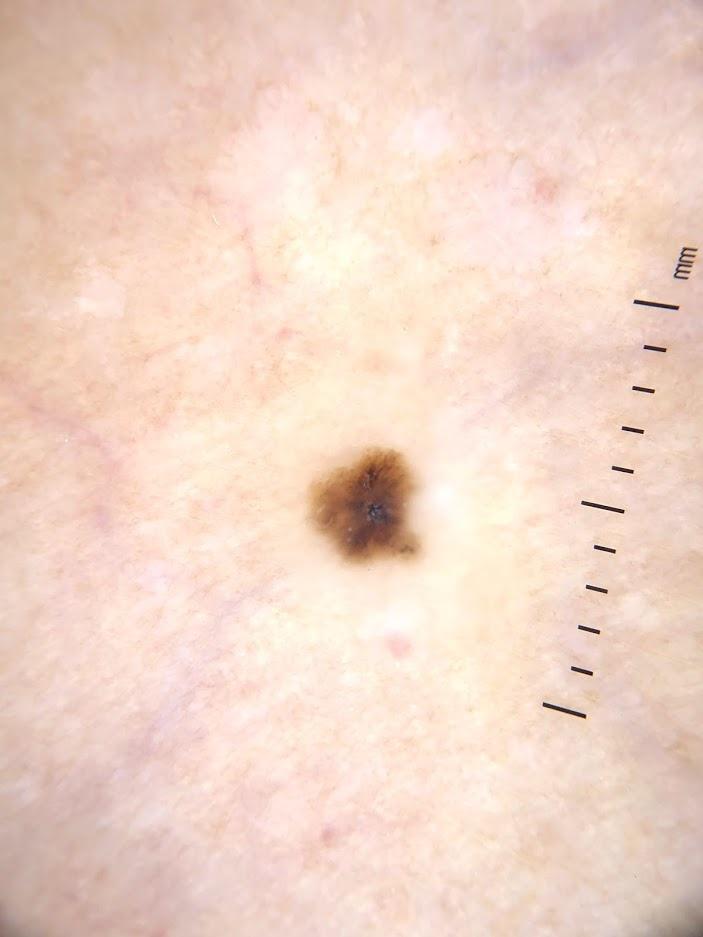imaging: contact-polarized dermoscopy
patient: female, approximately 55 years of age
location: a lower extremity
diagnostic label: Nevus (biopsy-proven)